Dermoscopy of a skin lesion.
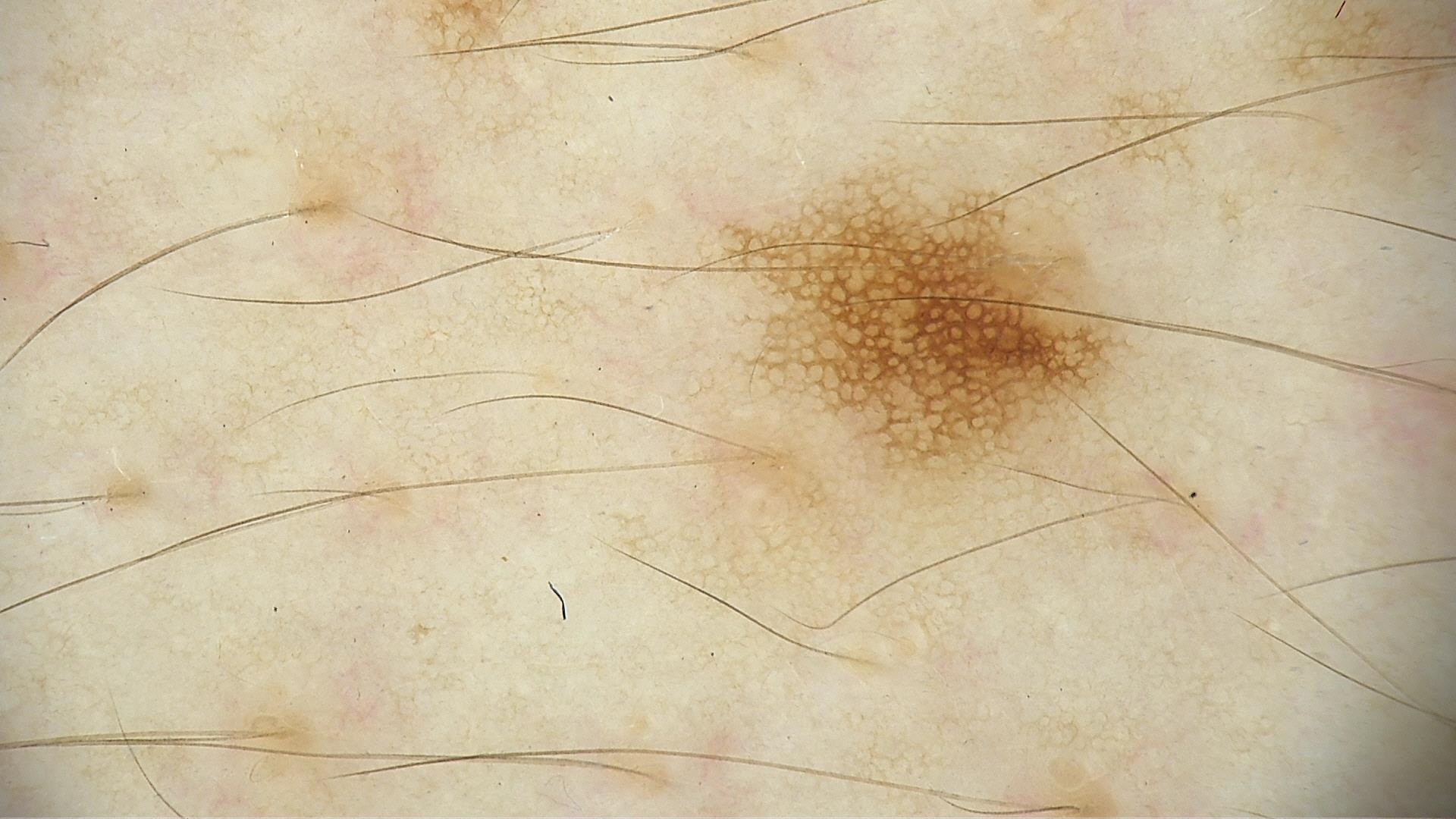Classified as a benign lesion — a dysplastic junctional nevus.